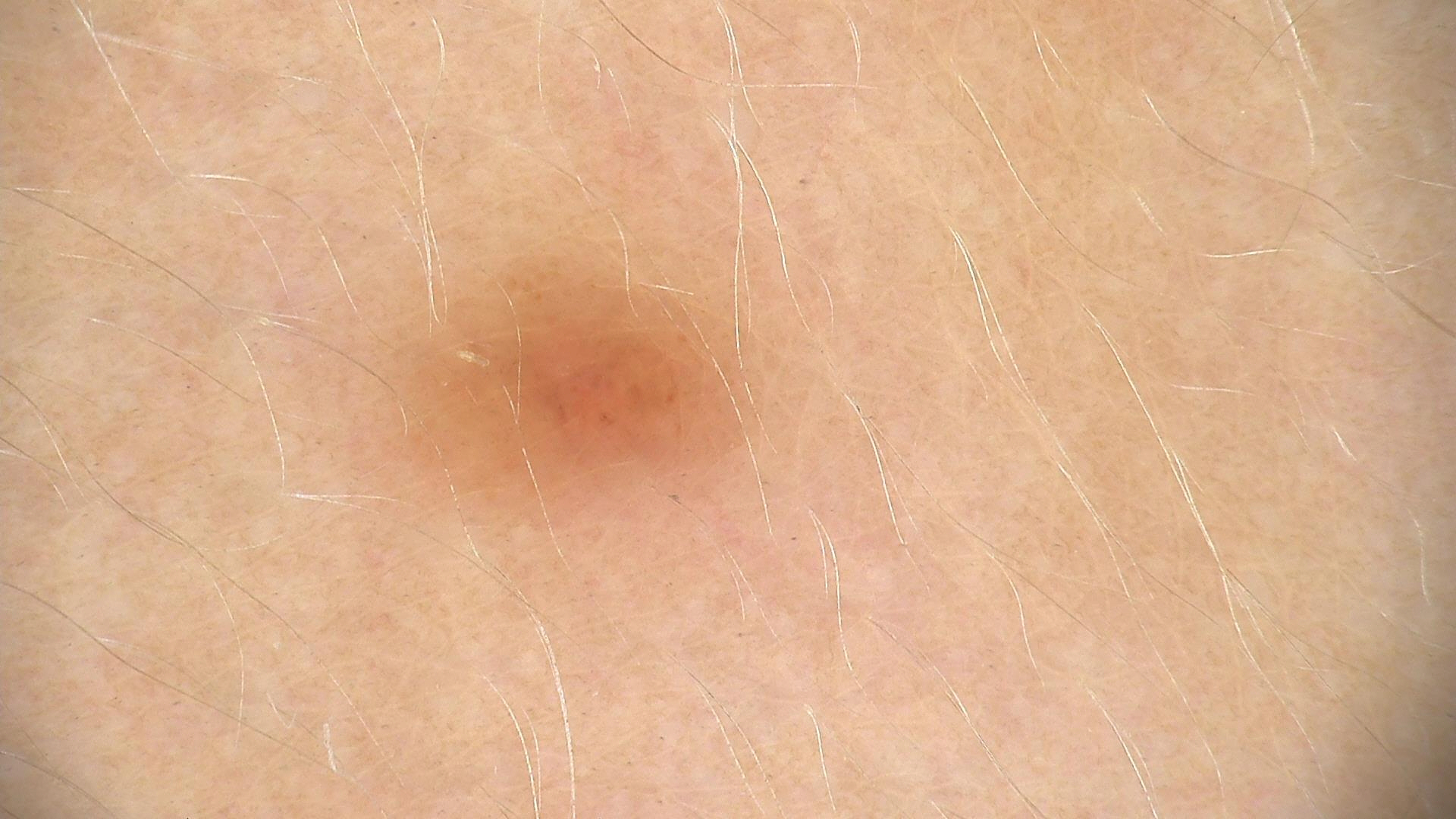diagnosis=junctional nevus (expert consensus).